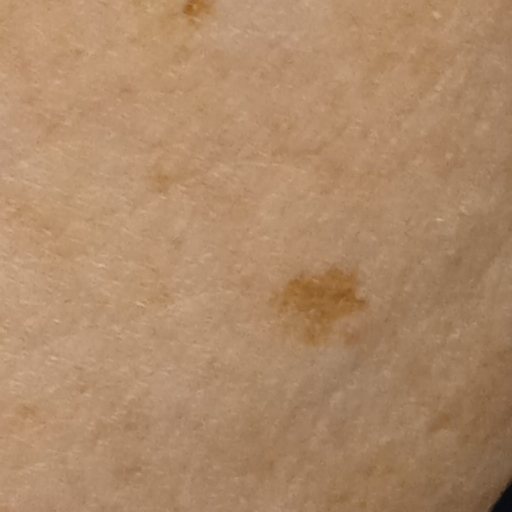Q: Patient demographics?
A: female, aged 71
Q: What is the referral context?
A: research study (no referral diagnosis)
Q: What kind of image is this?
A: clinical photo
Q: Where is the lesion?
A: an arm
Q: How large is the lesion?
A: 6.1 mm
Q: What was the diagnosis?
A: melanocytic nevus (dermatologist consensus)